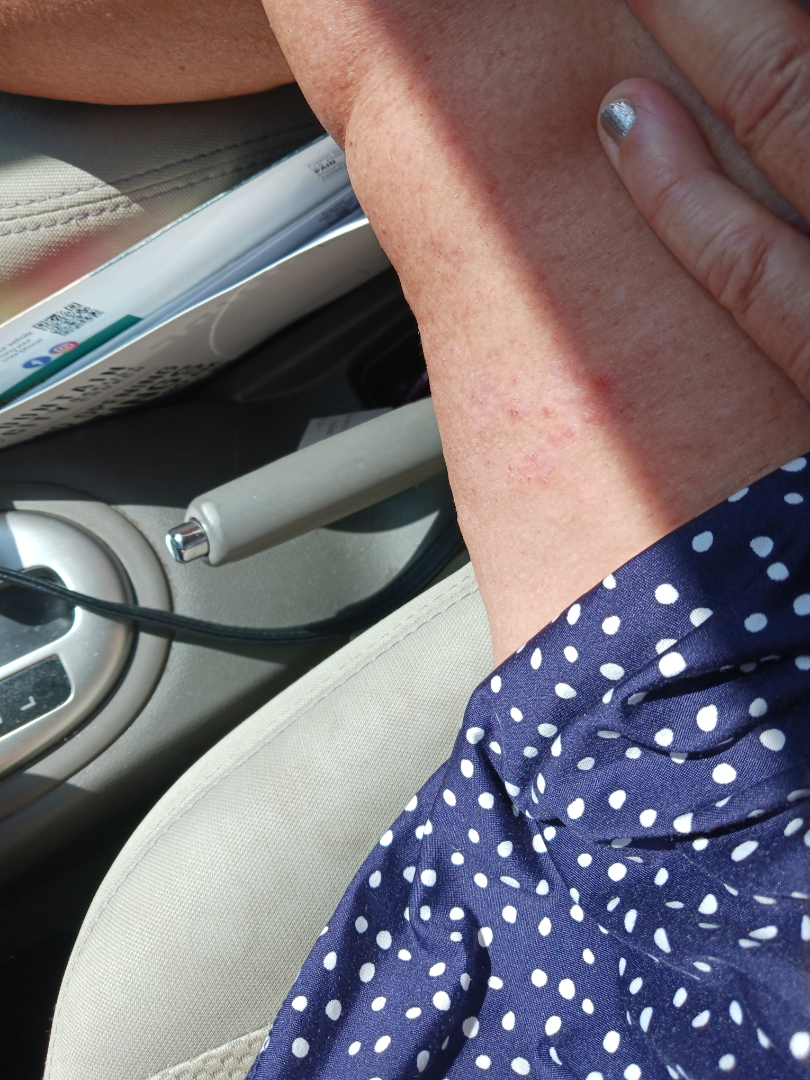anatomic site = leg | photo taken = at a distance | patient = female, age 60–69 | symptoms = bothersome appearance and itching | patient's own categorization = a rash | described texture = raised or bumpy and rough or flaky | impression = reviewed remotely by one dermatologist: in keeping with Eczema.